This image was taken at a distance; the contributor reports the condition has been present for one to four weeks; self-categorized by the patient as a rash; the lesion involves the leg; the lesion is described as flat; the contributor is 40–49, female; the contributor reports bothersome appearance: 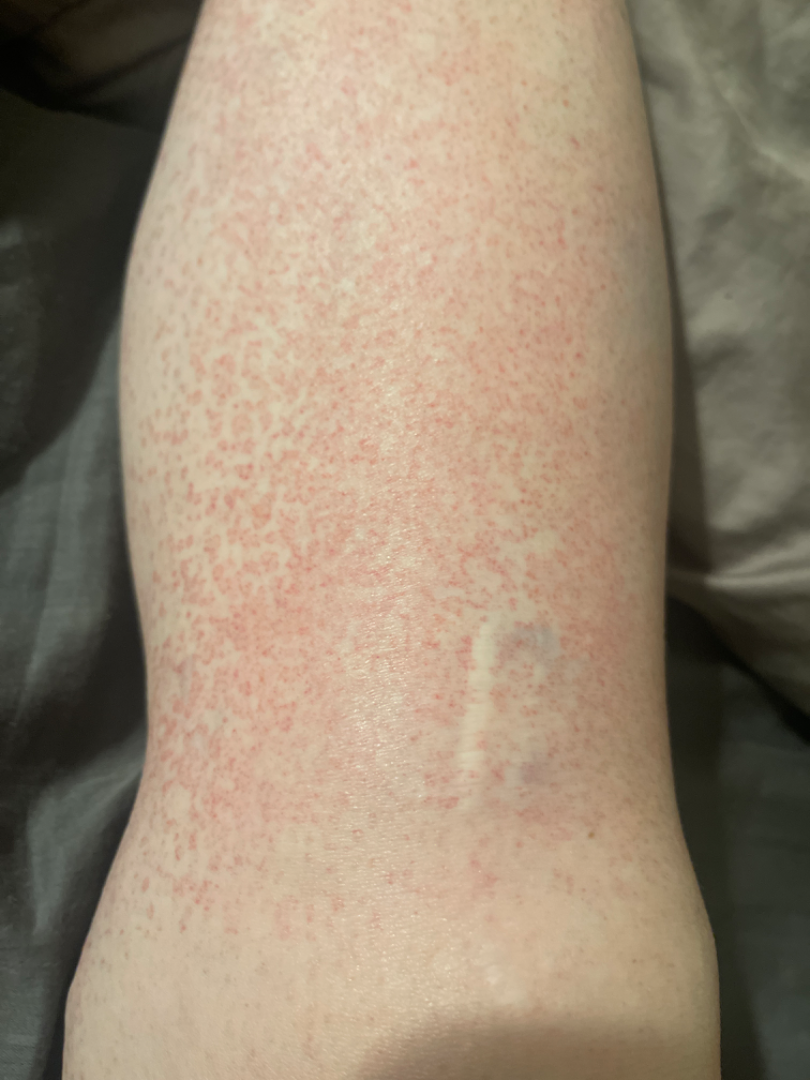Assessment:
One reviewing dermatologist: most consistent with Leukocytoclastic Vasculitis; also consider Pigmented purpuric eruption; lower on the differential is Hypersensitivity.